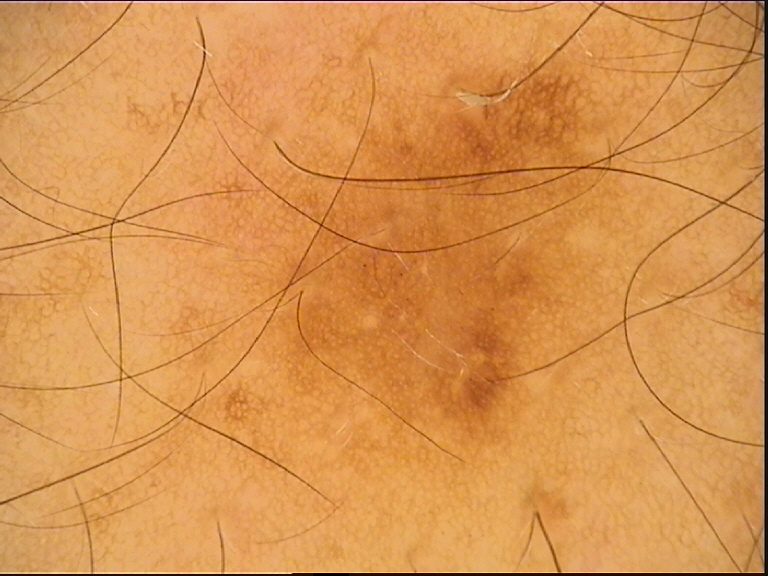Case:
A dermoscopic close-up of a skin lesion.
Conclusion:
The diagnostic label was a benign, fibro-histiocytic lesion — a dermatofibroma.